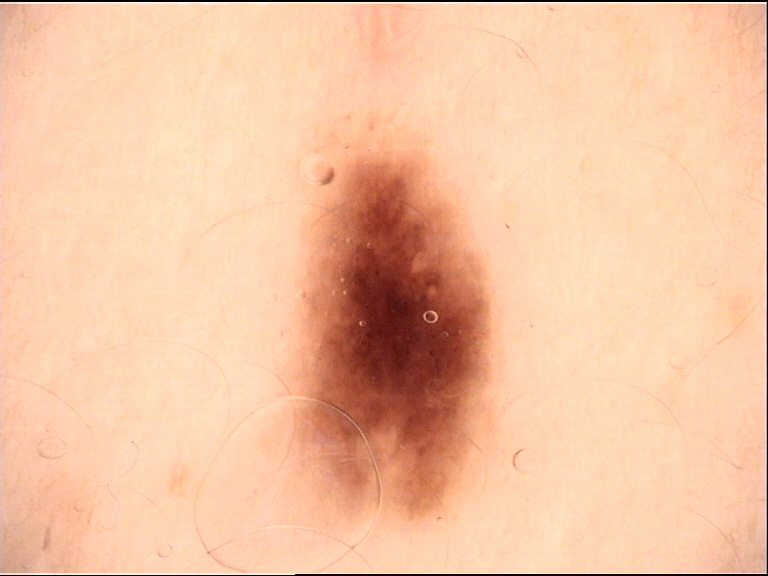  diagnosis:
    name: dysplastic junctional nevus
    code: jd
    malignancy: benign
    super_class: melanocytic
    confirmation: expert consensus